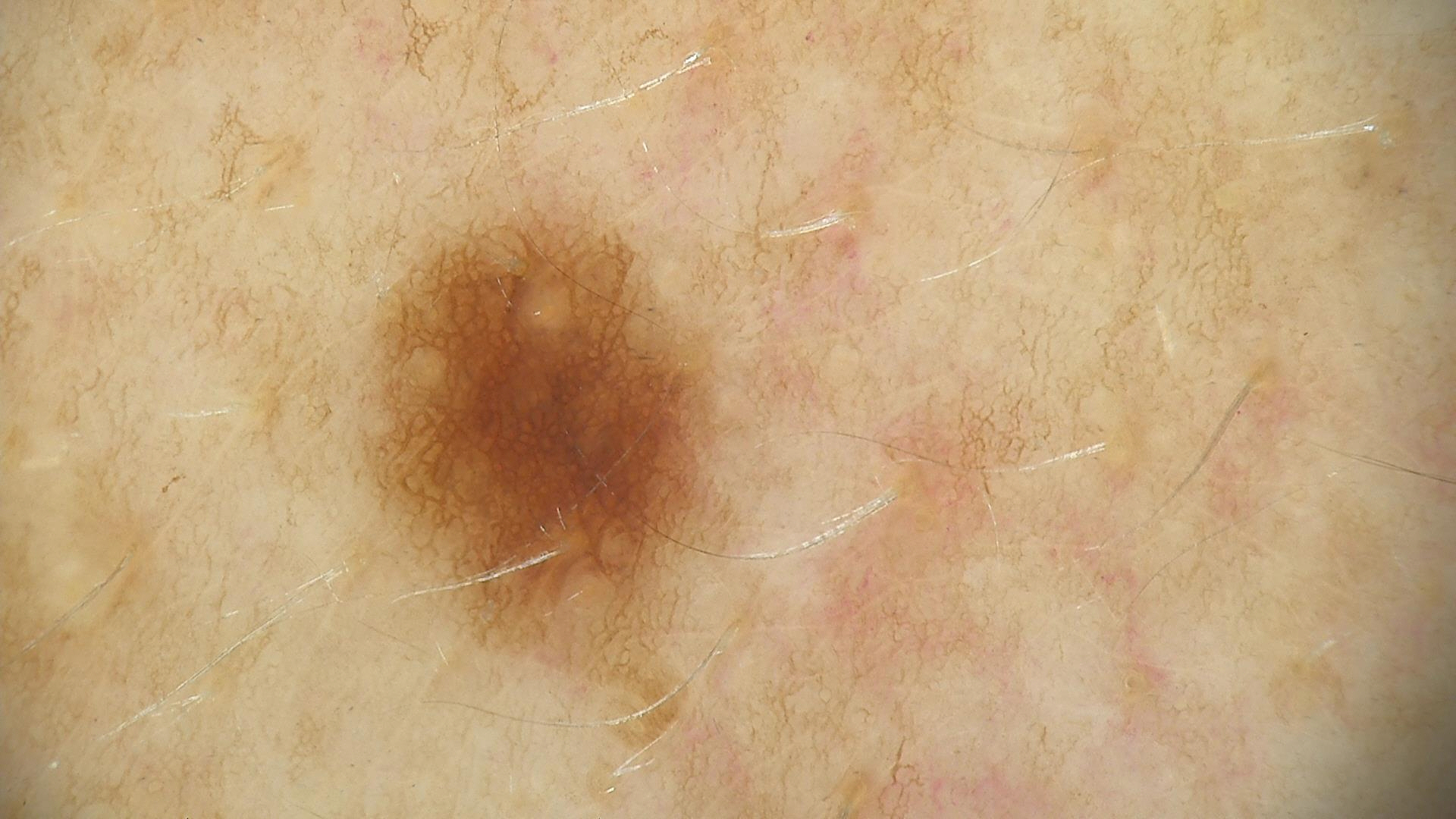Q: What is the diagnosis?
A: dysplastic junctional nevus (expert consensus)